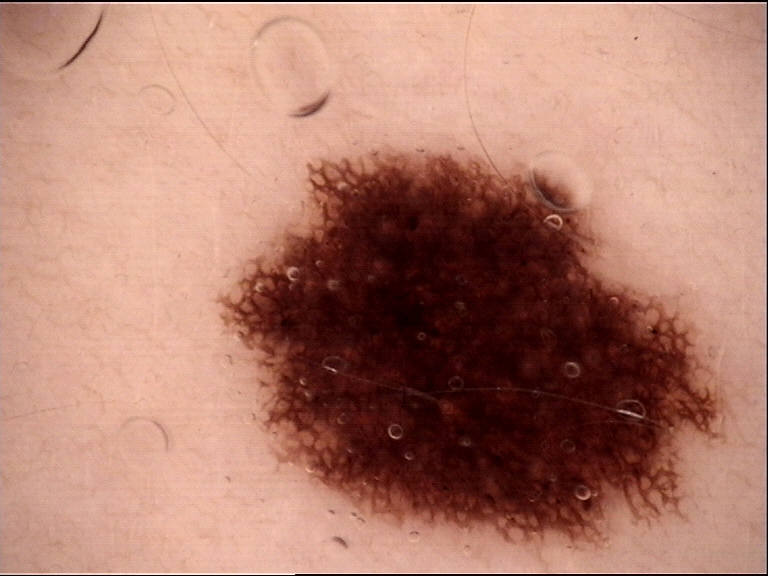The diagnosis was a benign lesion — a dysplastic compound nevus.